A dermoscopic close-up of a skin lesion.
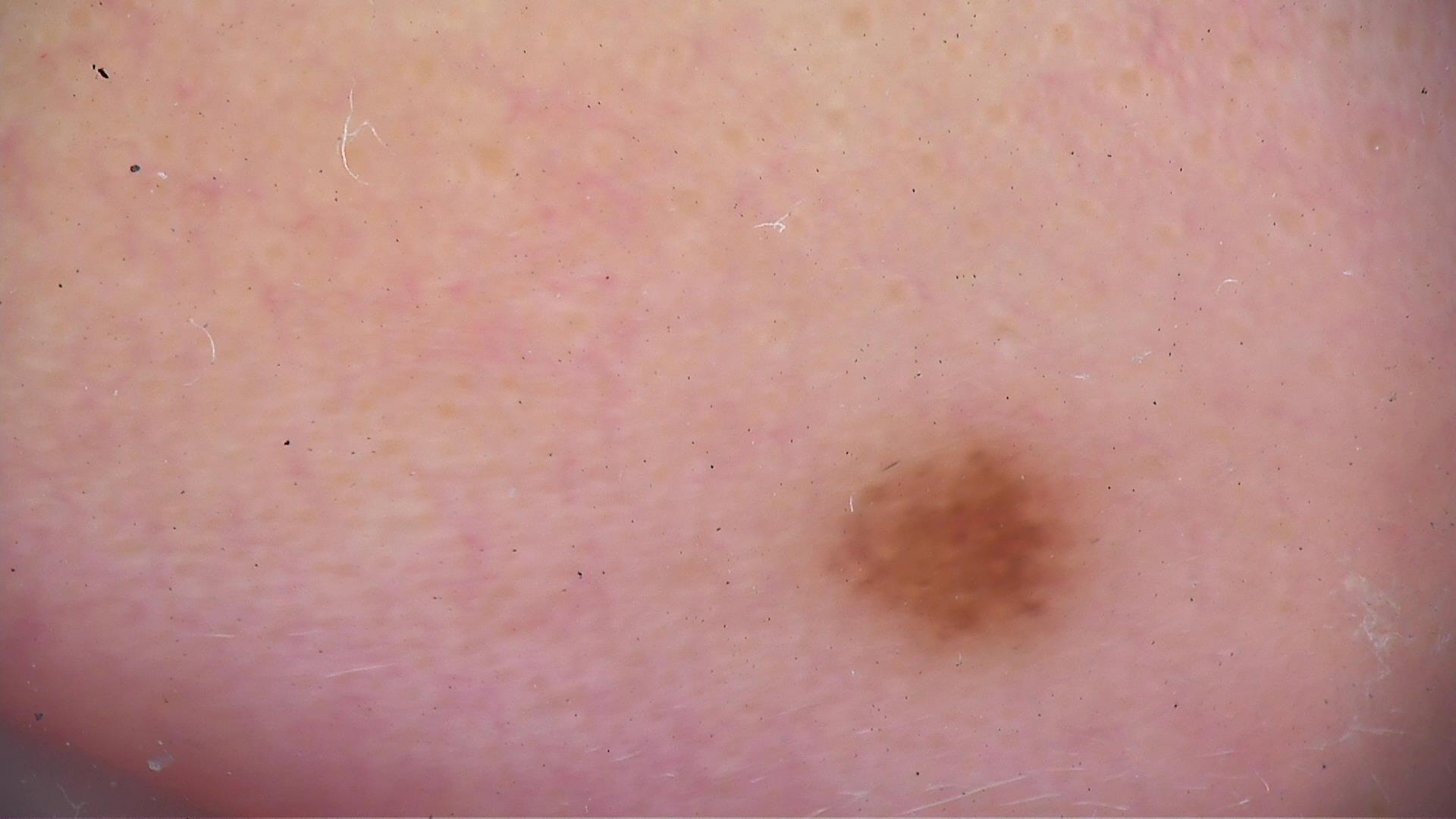| feature | finding |
|---|---|
| classification | compound, banal |
| label | Miescher nevus (expert consensus) |